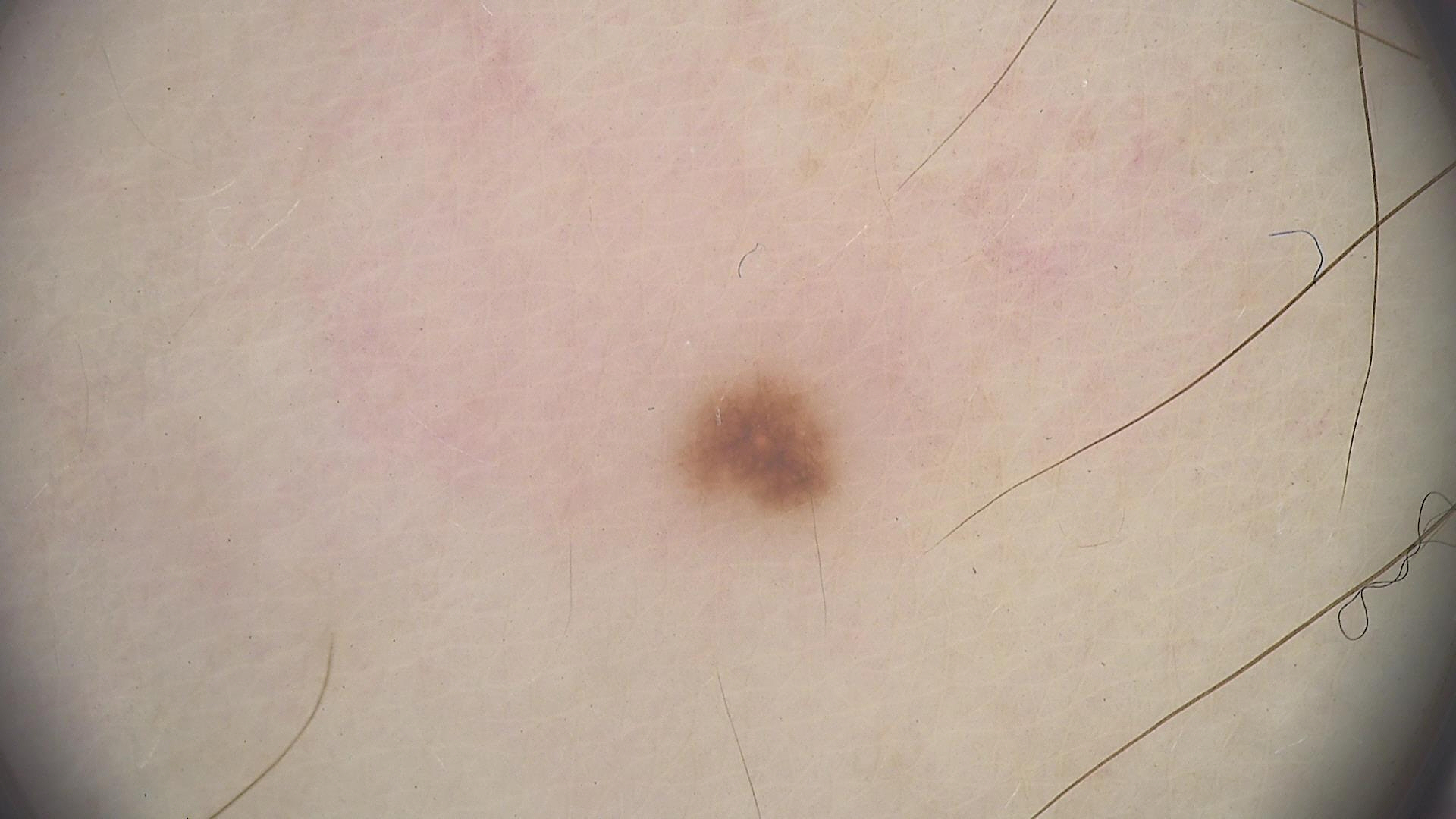modality: dermoscopy | assessment: dysplastic junctional nevus (expert consensus).